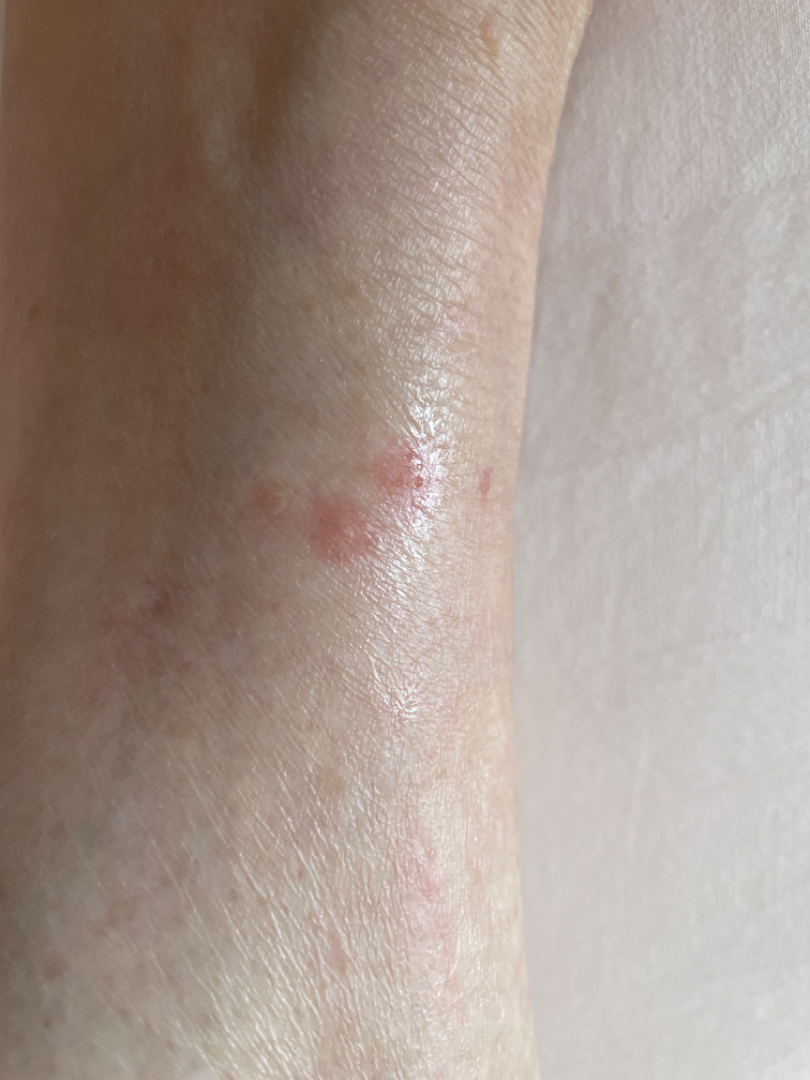<summary>
  <assessment>could not be assessed</assessment>
</summary>